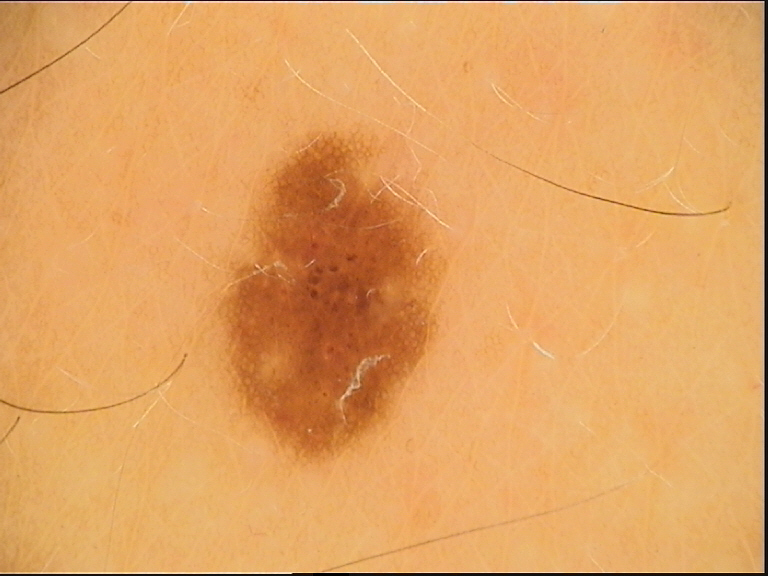Consistent with a dysplastic junctional nevus.